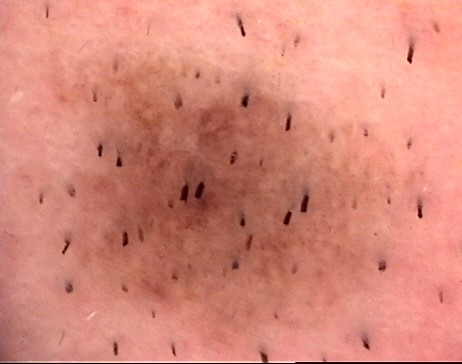<lesion>
  <diagnosis>
    <name>Miescher nevus</name>
    <code>mcb</code>
    <malignancy>benign</malignancy>
    <super_class>melanocytic</super_class>
    <confirmation>expert consensus</confirmation>
  </diagnosis>
</lesion>